The patient indicates associated shortness of breath · skin tone: Fitzpatrick II · texture is reported as rough or flaky · male subject, age 40–49 · the head or neck is involved · the patient considered this a rash · reported duration is one to four weeks · the photograph was taken at a distance: 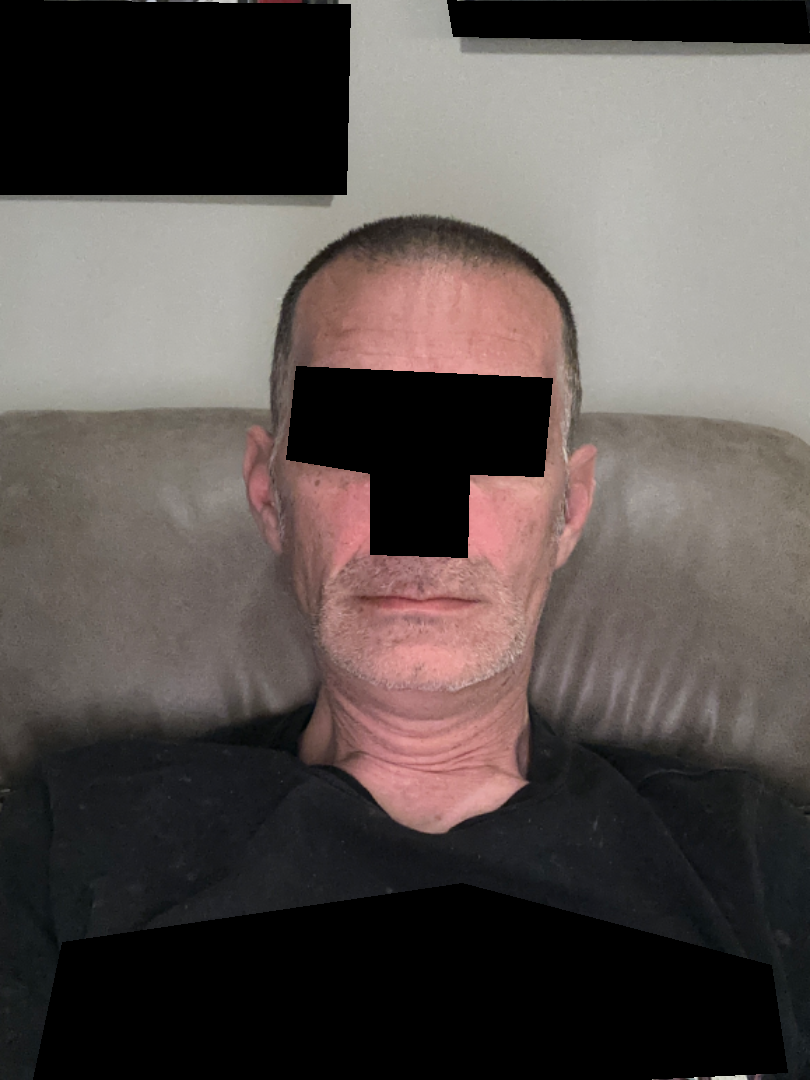assessment: no findings on review.